The lesion is described as raised or bumpy · the patient considered this a rash · reported duration is one to four weeks · the back of the hand and arm are involved · female subject, age 18–29 · skin tone: Fitzpatrick II; lay graders estimated 2 on the Monk Skin Tone · the photograph was taken at an angle · symptoms reported: enlargement, itching and bothersome appearance: 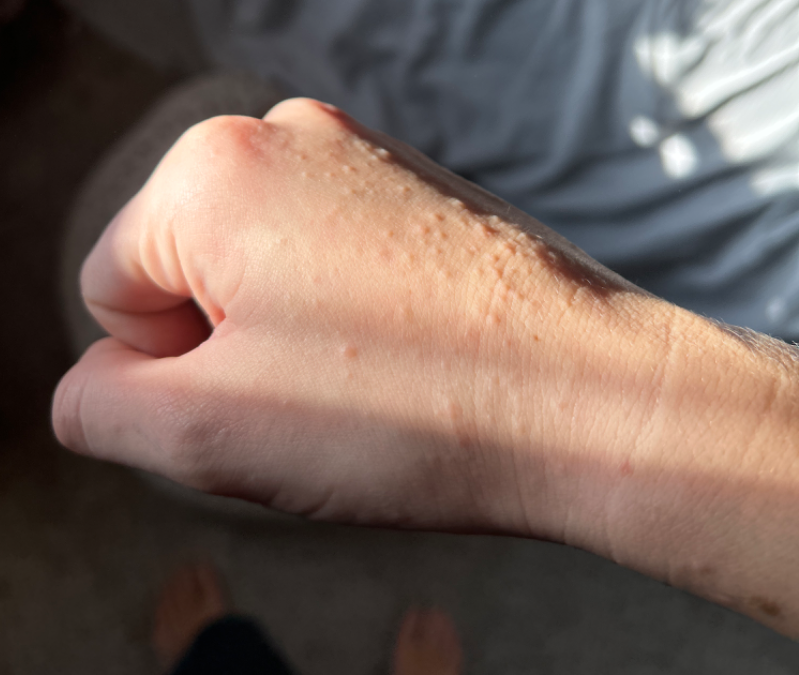Q: What is the dermatologist's impression?
A: single-reviewer assessment: the primary impression is Lichen nitidus; also consider Eczema